The patient described the issue as a rash. The patient notes the condition has been present for three to twelve months. The patient notes bleeding, itching, bothersome appearance and burning. The affected area is the leg. The photograph is a close-up of the affected area. The patient notes the lesion is raised or bumpy. Associated systemic symptoms include fatigue and mouth sores. The subject is a female aged 70–79.
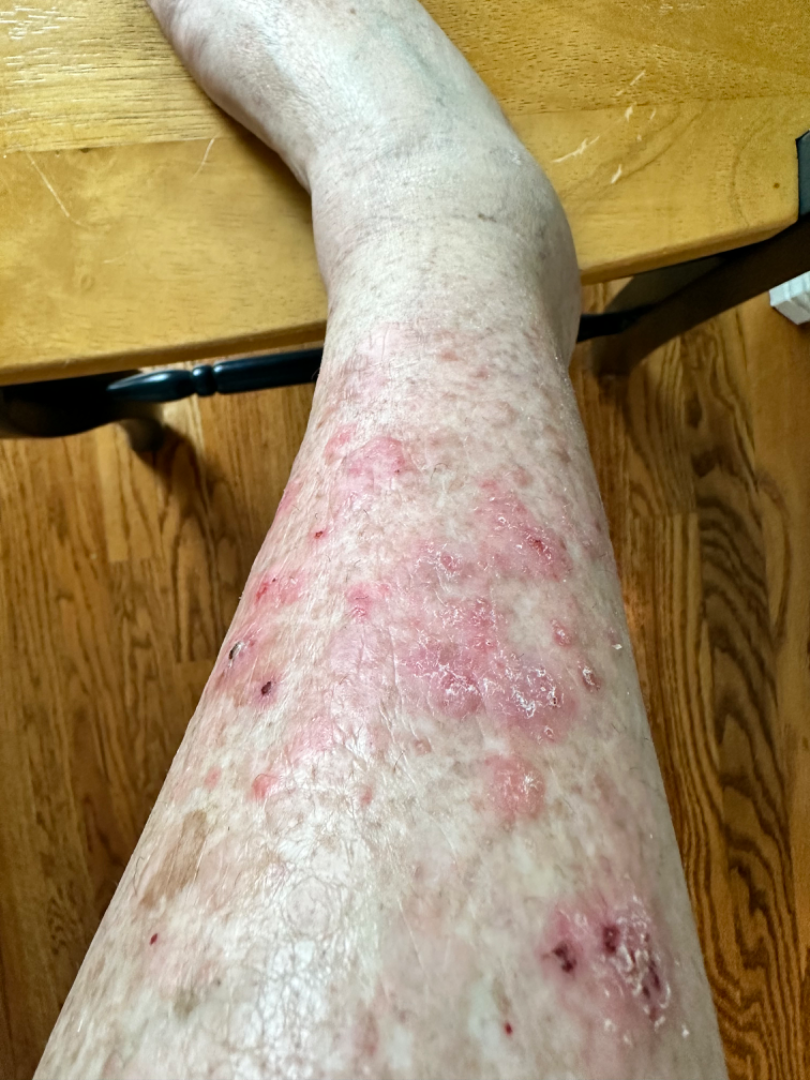On remote review of the image: most consistent with Lichen Simplex Chronicus; also raised was Lichen planus/lichenoid eruption; possibly Chronic dermatitis, NOS.